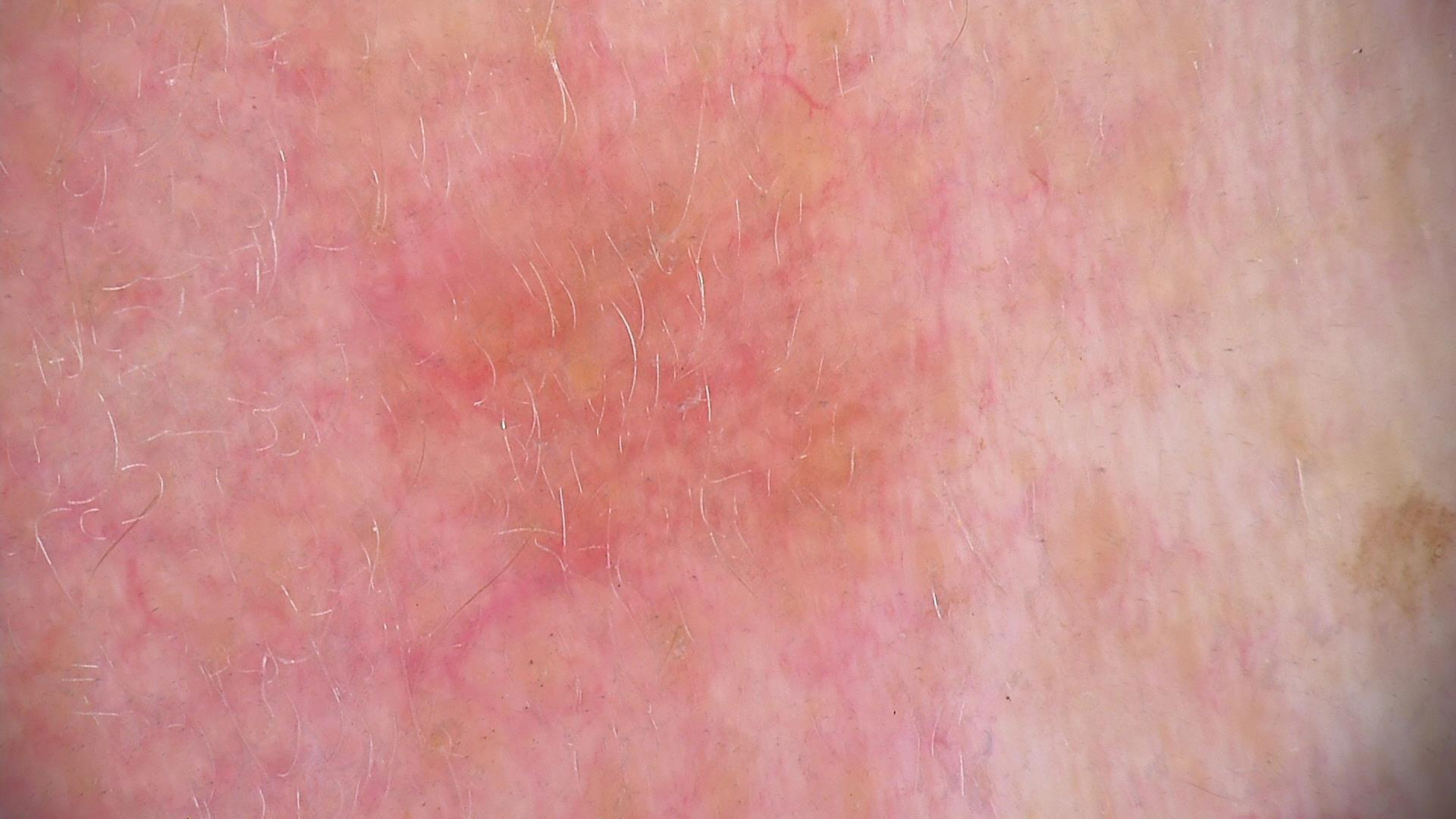diagnosis: actinic keratosis (expert consensus)